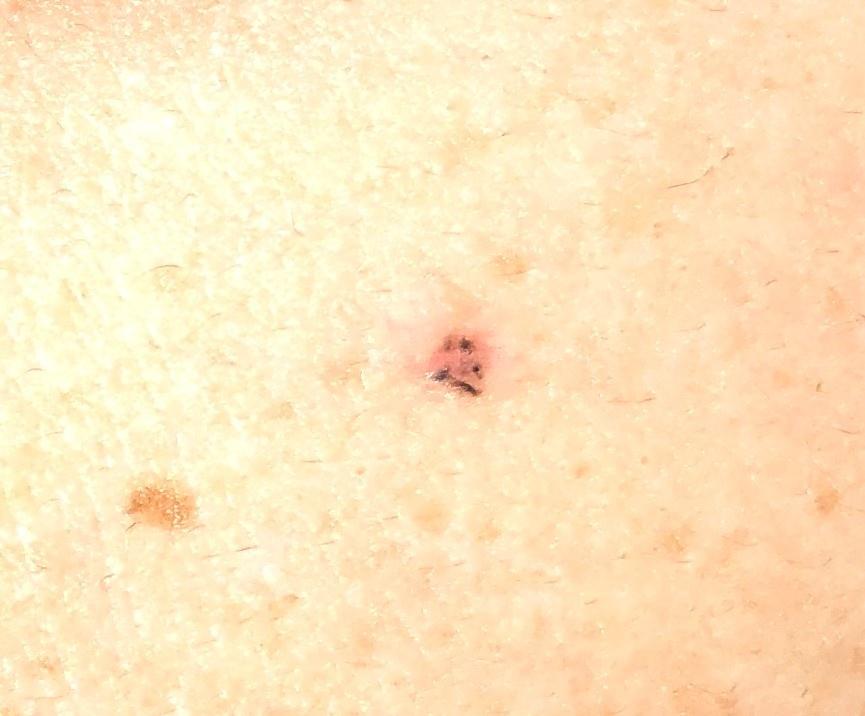Findings:
– diagnostic label — Basal cell carcinoma (biopsy-proven)